Located on the leg. The photograph is a close-up of the affected area. Female contributor, age 40–49: 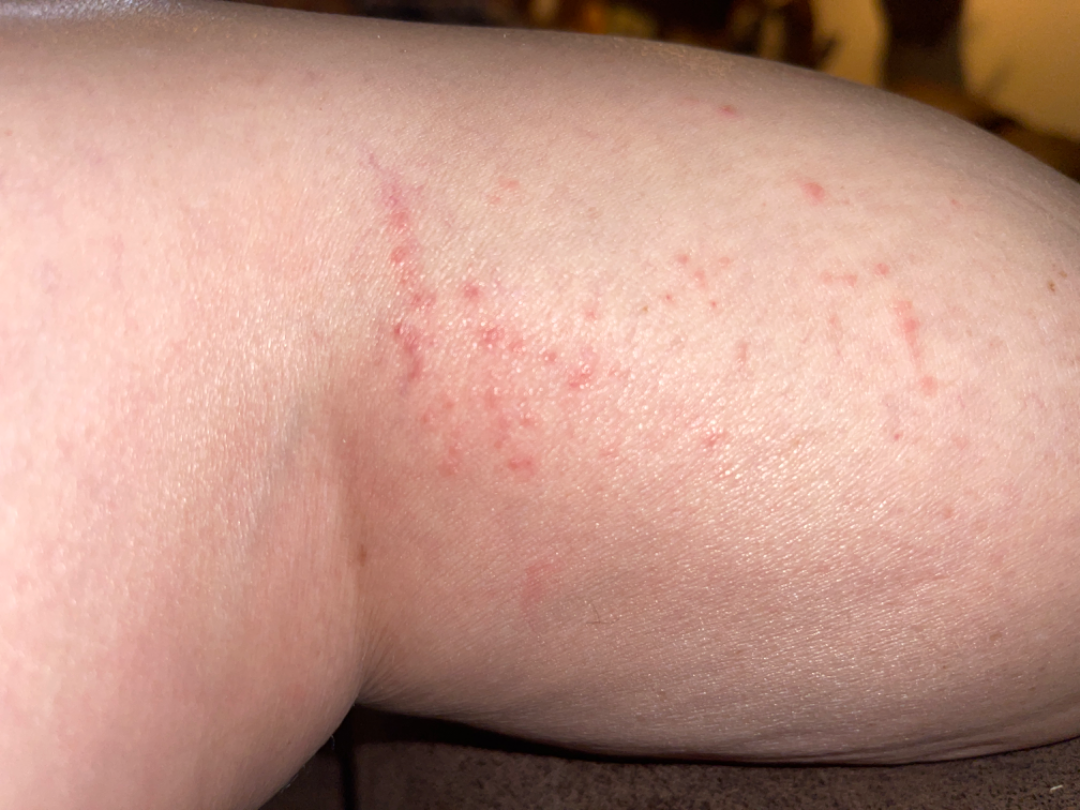Q: Could the case be diagnosed?
A: ungradable on photographic review
Q: When did this start?
A: less than one week
Q: Patient's own categorization?
A: a rash